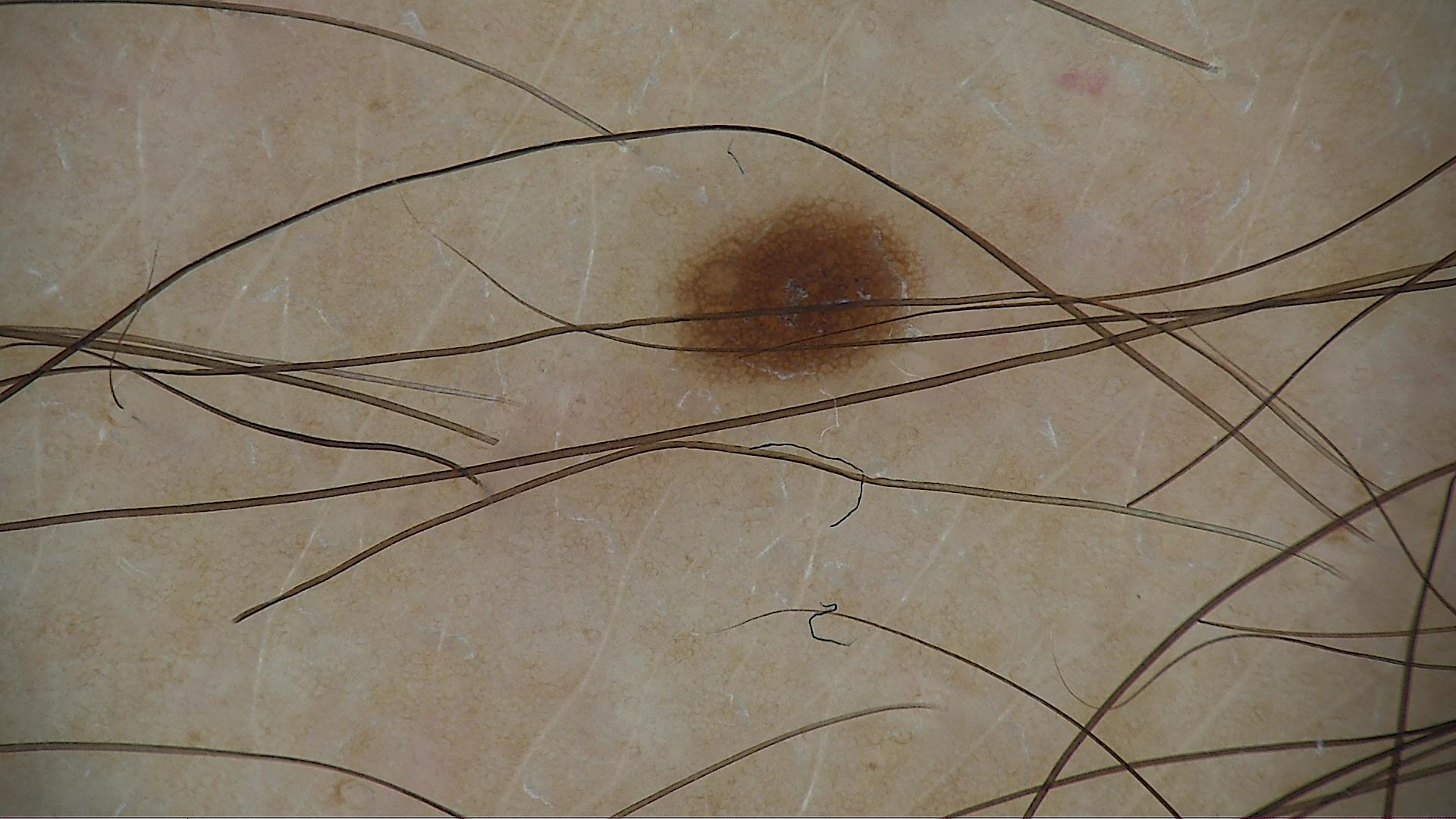A dermoscopy image of a single skin lesion.
The architecture is that of a banal lesion.
The diagnosis was a junctional nevus.